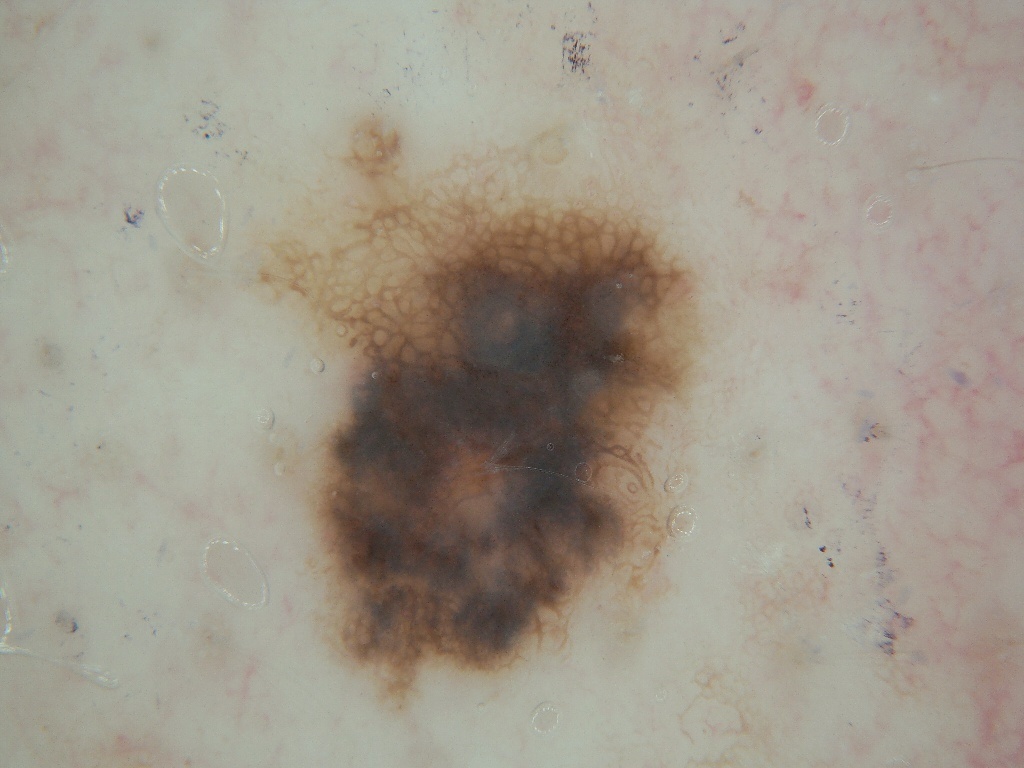Summary:
A skin lesion imaged with a dermatoscope. The lesion is located at <box>243, 112, 706, 719</box>. Dermoscopic examination shows neither globules nor streaks. A mid-sized lesion within the field.
Assessment:
Expert review diagnosed this as a benign lesion.